A dermatoscopic image of a skin lesion: 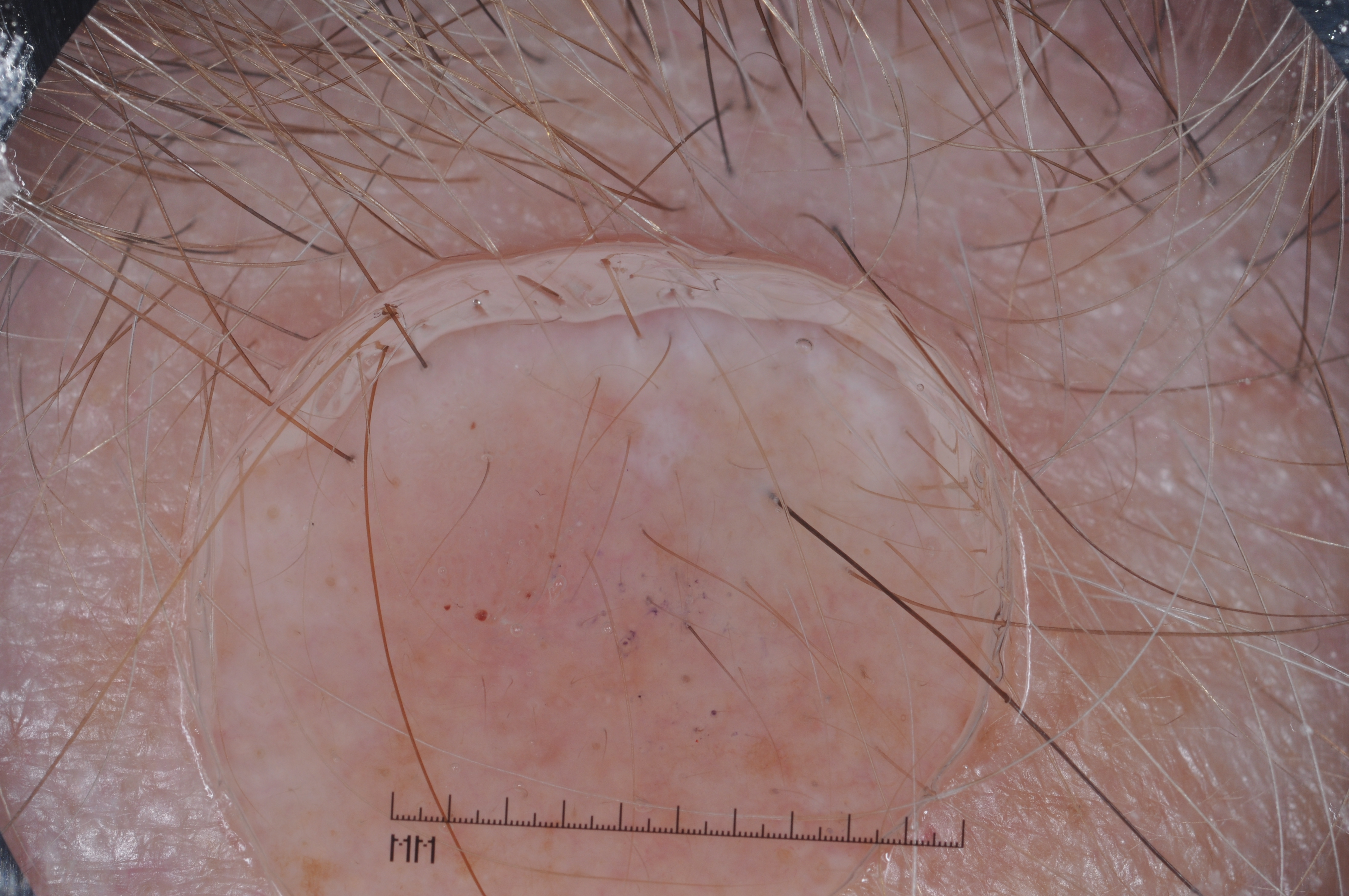The lesion's extent is 333/363/658/674. Dermoscopic examination shows milia-like cysts. Clinically diagnosed as a seborrheic keratosis, a benign lesion.